The subject is a female aged 18–29; located on the leg; this is a close-up image.
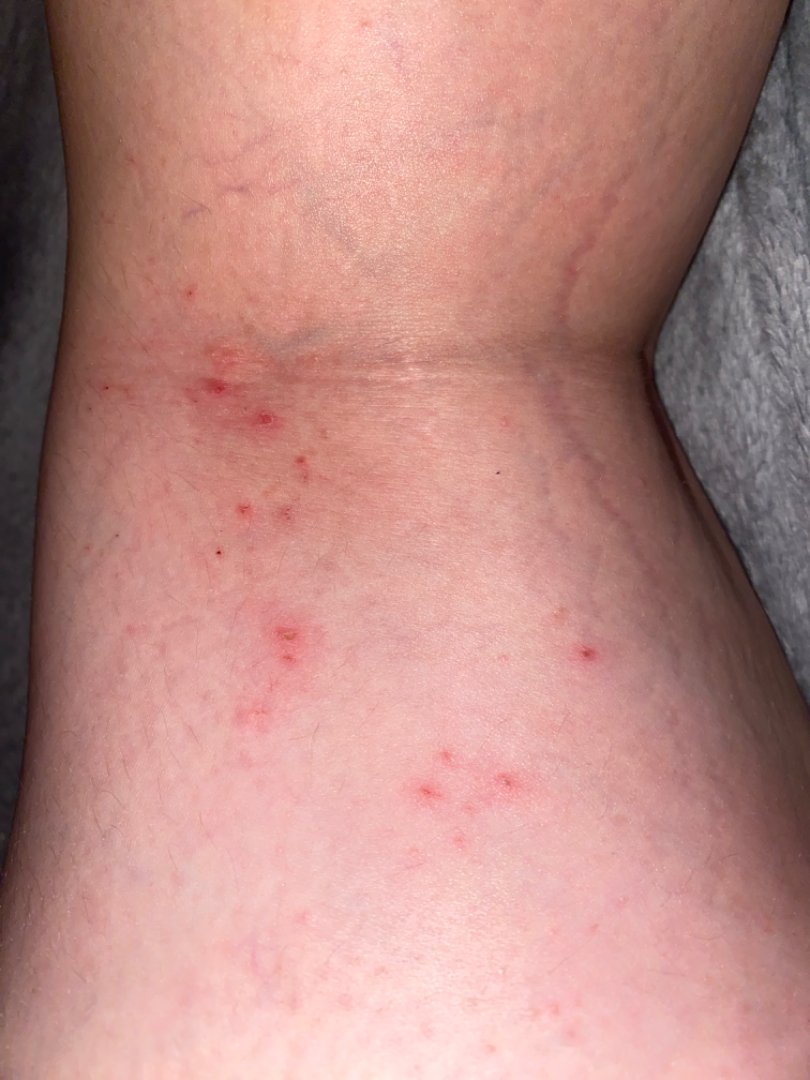Q: Fitzpatrick or Monk tone?
A: Fitzpatrick skin type III; human graders estimated Monk skin tone scale 2
Q: Patient's own categorization?
A: a rash
Q: Reported symptoms?
A: itching
Q: How long has this been present?
A: less than one week
Q: Constitutional symptoms?
A: none reported
Q: What is the differential diagnosis?
A: a single dermatologist reviewed the case: the differential includes Eczema and Acute dermatitis, NOS, with no clear leading consideration